A skin lesion imaged with a dermatoscope, the subject is a male aged 33 to 37: 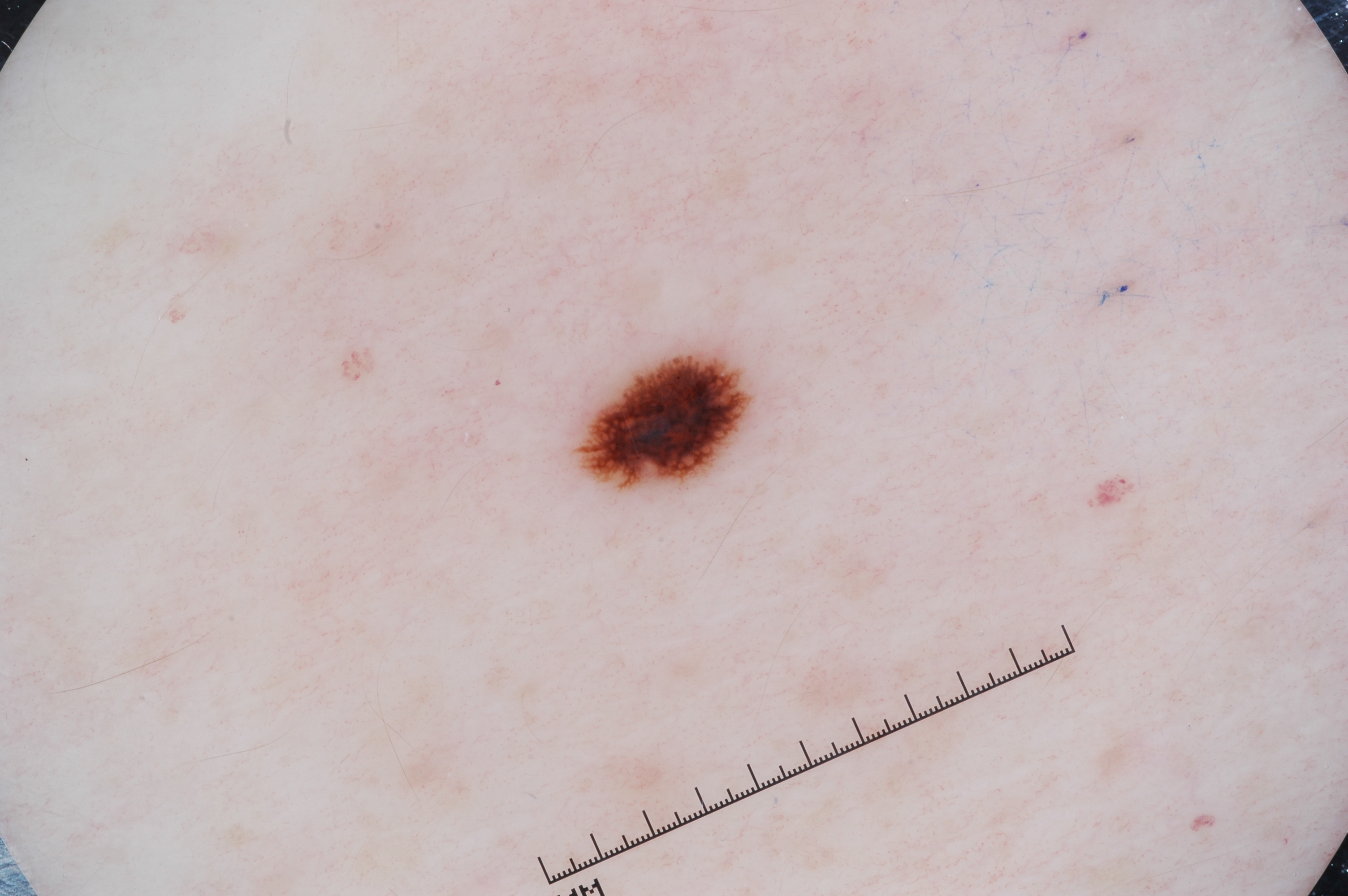Findings:
• extent — small
• location — box(579, 350, 747, 490)
• features — streaks and pigment network
• impression — a melanoma